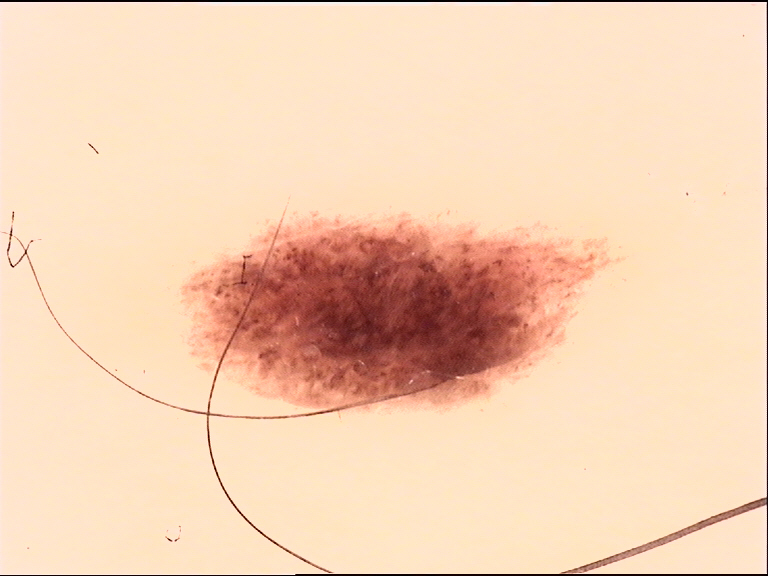Q: What kind of image is this?
A: dermatoscopy
Q: What was the diagnostic impression?
A: dysplastic junctional nevus (expert consensus)